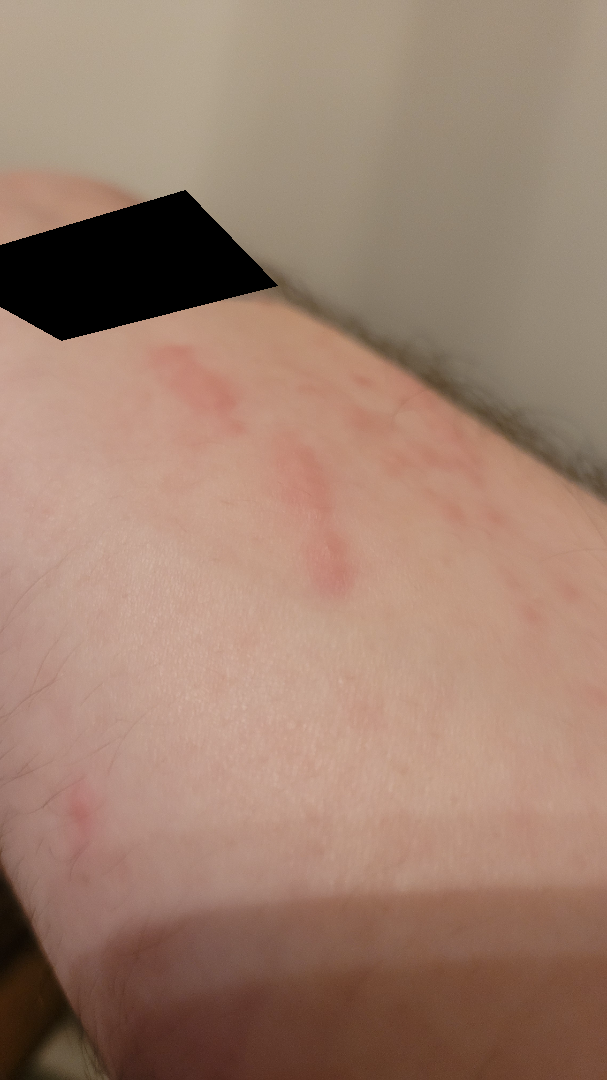Notes:
– assessment: indeterminate from the photograph
– image framing: at an angle